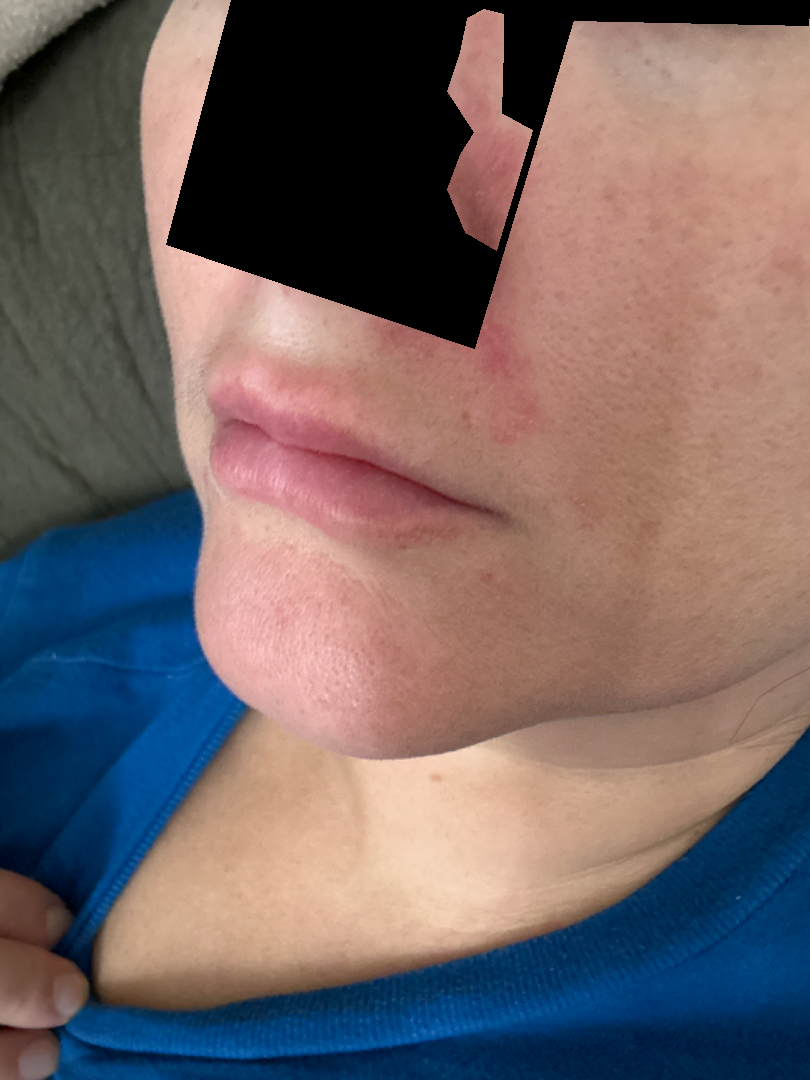{
  "differential": {
    "leading": [
      "Perioral Dermatitis"
    ]
  }
}